Male patient, age 50–59; close-up view; the affected area is the arm.
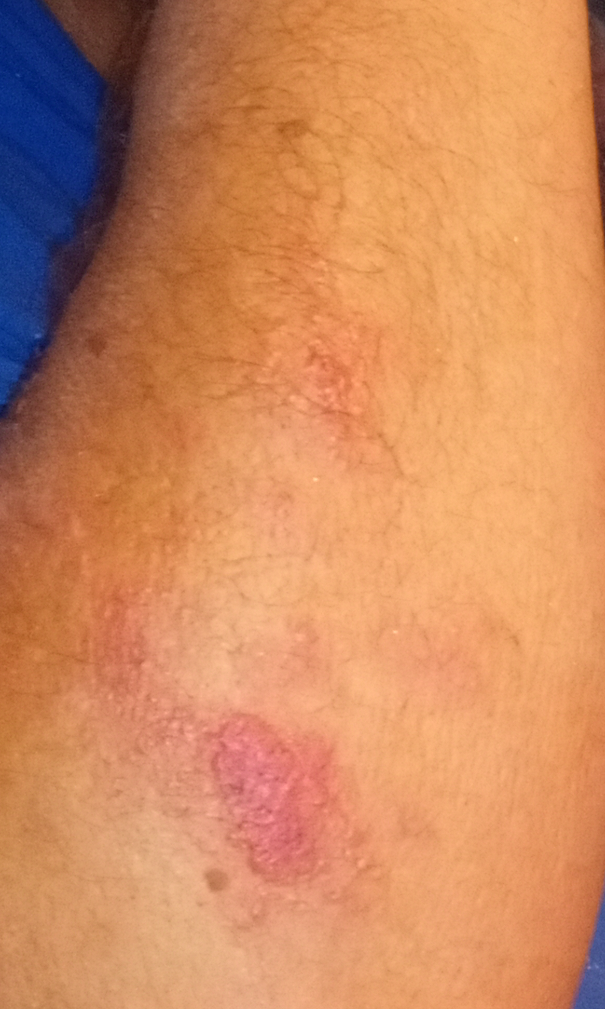surface texture = raised or bumpy | symptom duration = less than one week | skin tone = FST III; lay graders estimated Monk skin tone scale 3 or 5 | lesion symptoms = none reported | systemic symptoms = fatigue and fever | patient's own categorization = a rash | diagnostic considerations = consistent with Contact dermatitis.